The lesion involves the leg; the photo was captured at an angle: 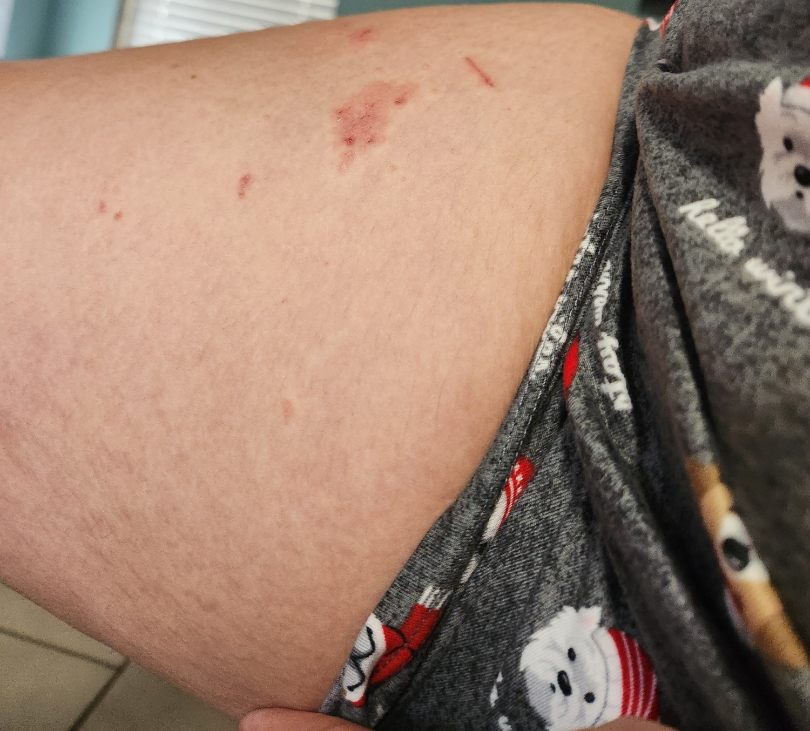Findings: On photographic review by a dermatologist, most likely Allergic Contact Dermatitis; also on the differential is Eczema; possibly Psoriasis.